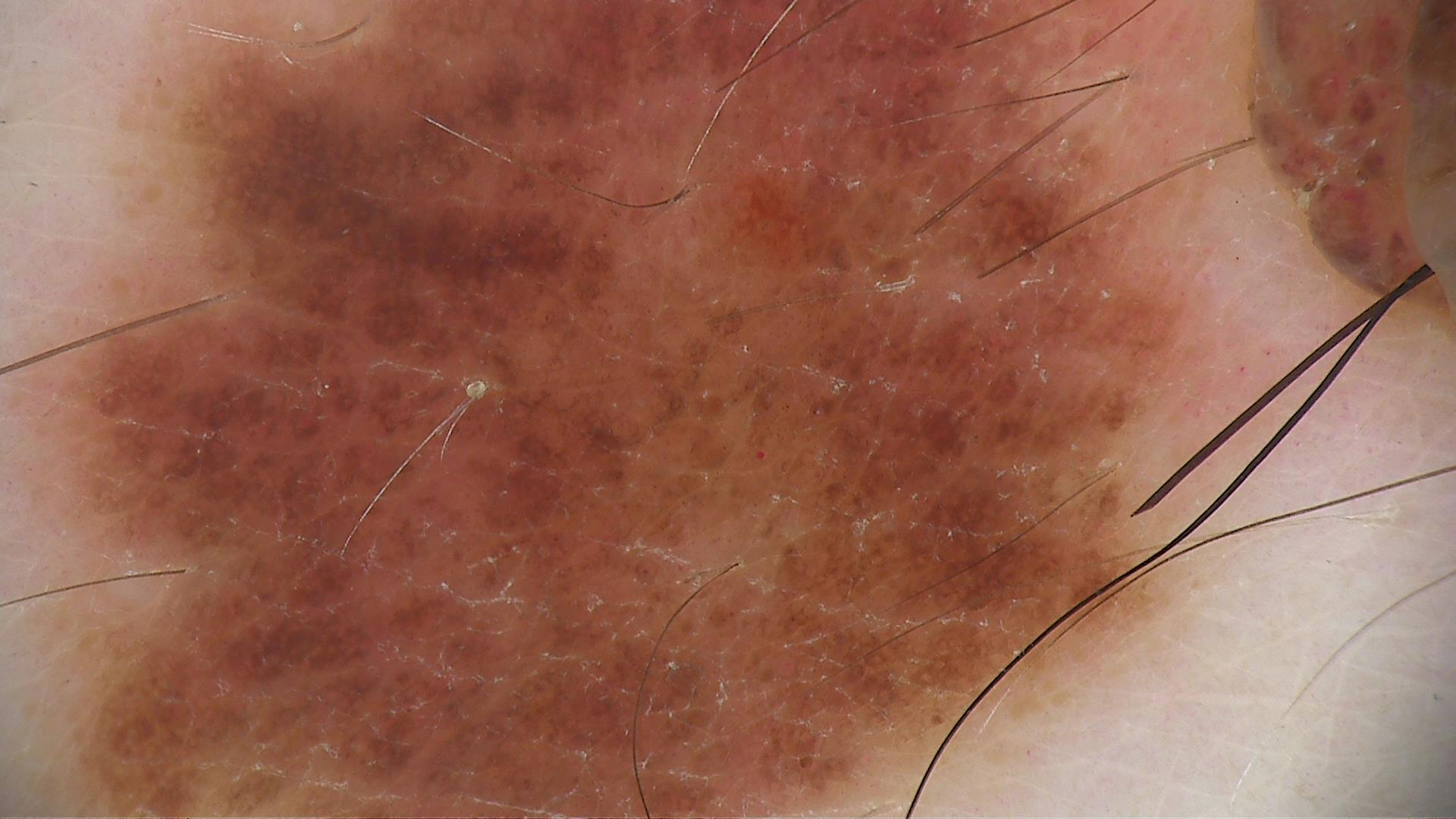The diagnosis was a dysplastic junctional nevus.